A dermoscopic image of a skin lesion.
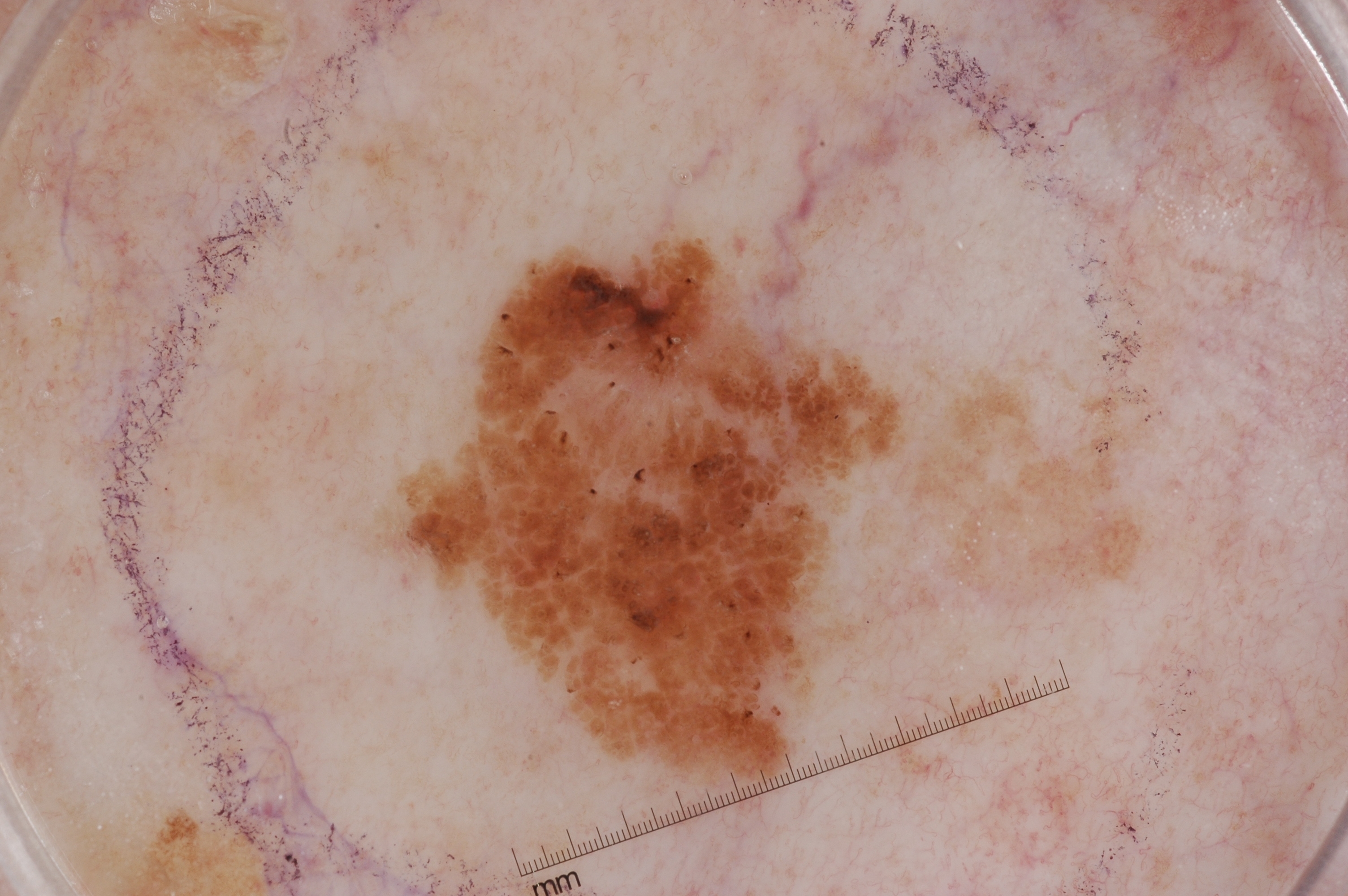lesion extent — ~12% of the field
dermoscopic features — negative network; absent: streaks, milia-like cysts, and pigment network
lesion location — 406/239/898/785
diagnosis — a seborrheic keratosis, a benign skin lesion